A close-up photograph:
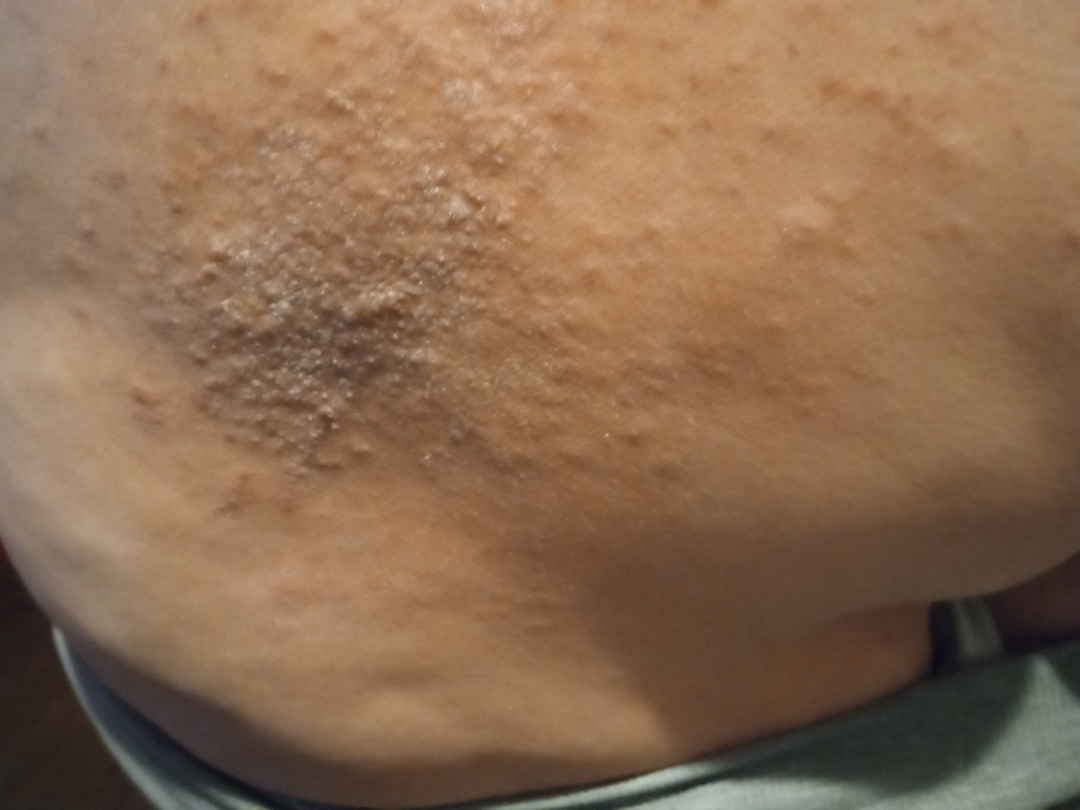{"skin_tone": {"fitzpatrick": "IV", "monk_skin_tone": 3}, "differential": {"tied_lead": ["Psoriasis", "Lichen Simplex Chronicus"]}}